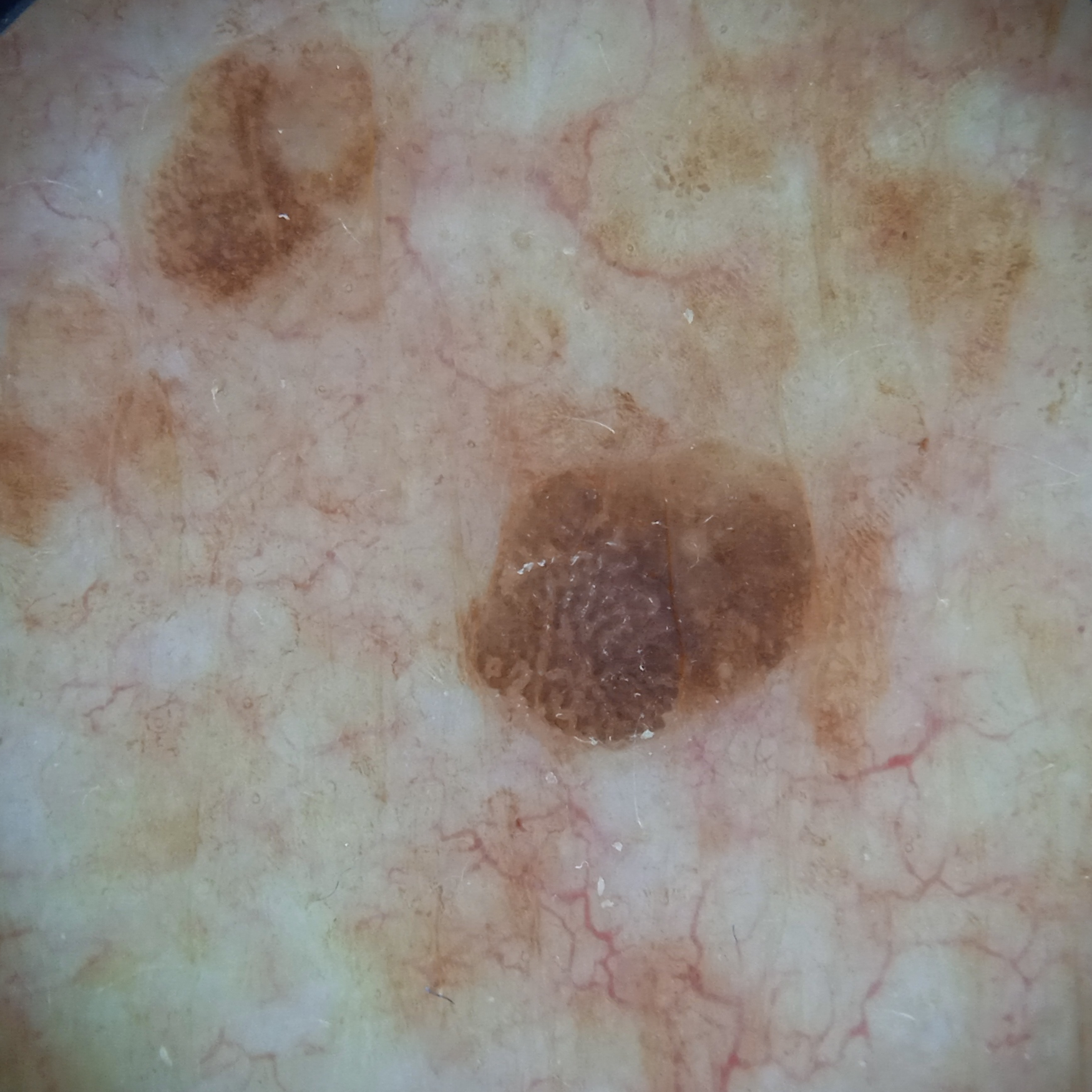Q: Why was this imaged?
A: research study (no referral diagnosis)
Q: Tell me about the patient.
A: female, age 84
Q: What is the patient's nevus burden?
A: few melanocytic nevi overall
Q: What are the relevant risk factors?
A: a personal history of cancer
Q: What is the anatomic site?
A: the torso
Q: Lesion size?
A: 4.6 mm
Q: What was the diagnosis?
A: seborrheic keratosis (dermatologist consensus)